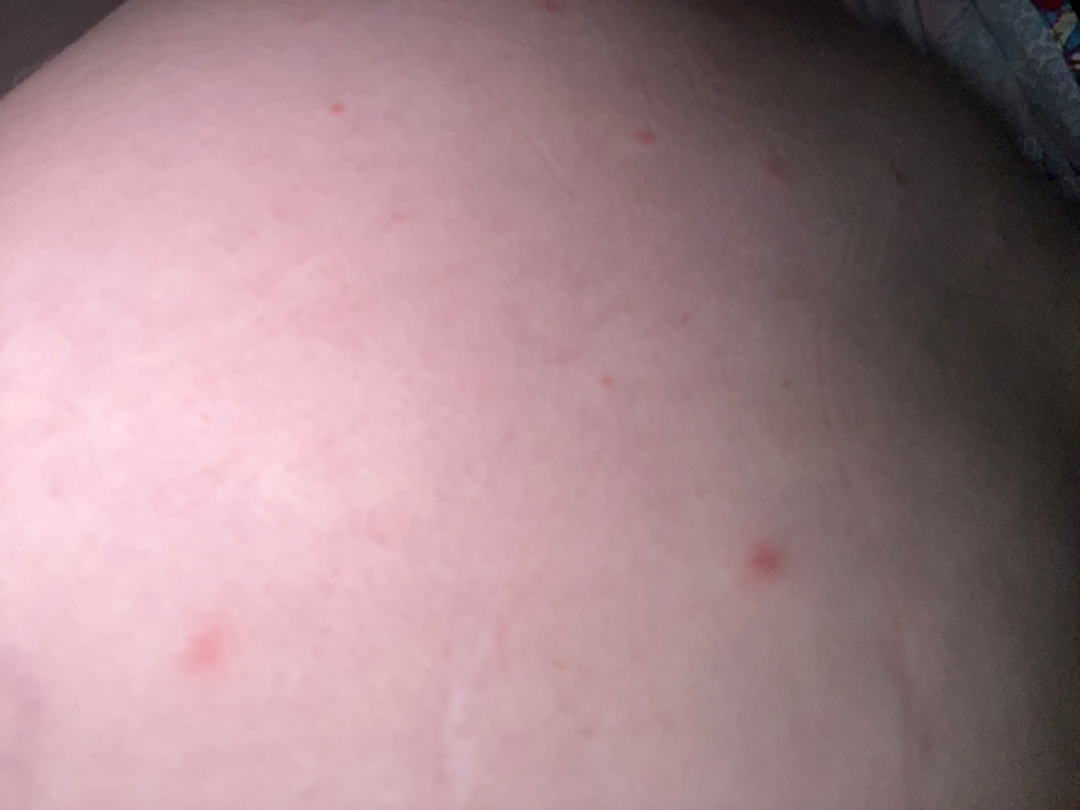Assessment:
The image was not sufficient for the reviewer to characterize the skin condition.